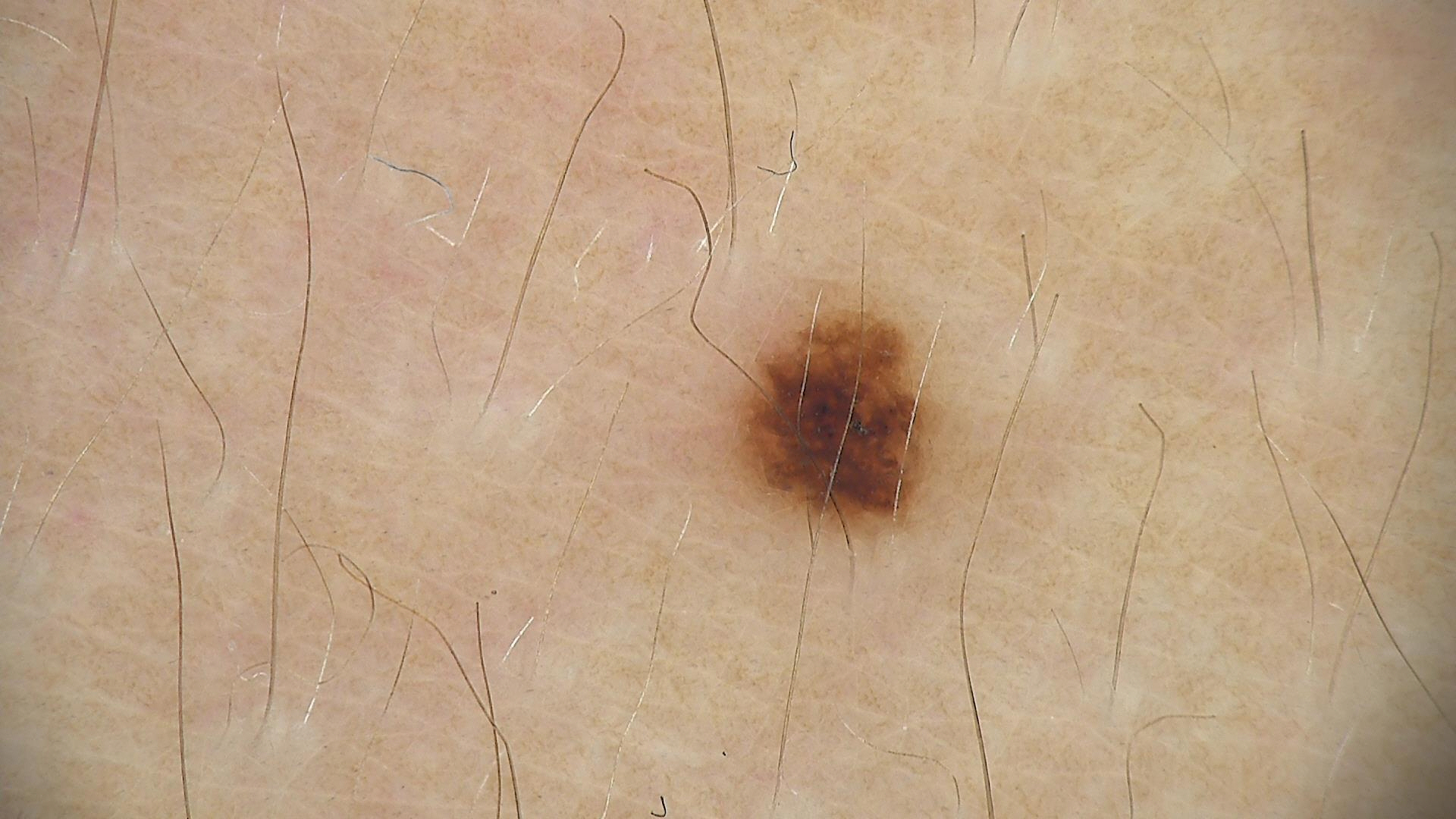A dermoscopic photograph of a skin lesion. Diagnosed as a benign lesion — a dysplastic junctional nevus.